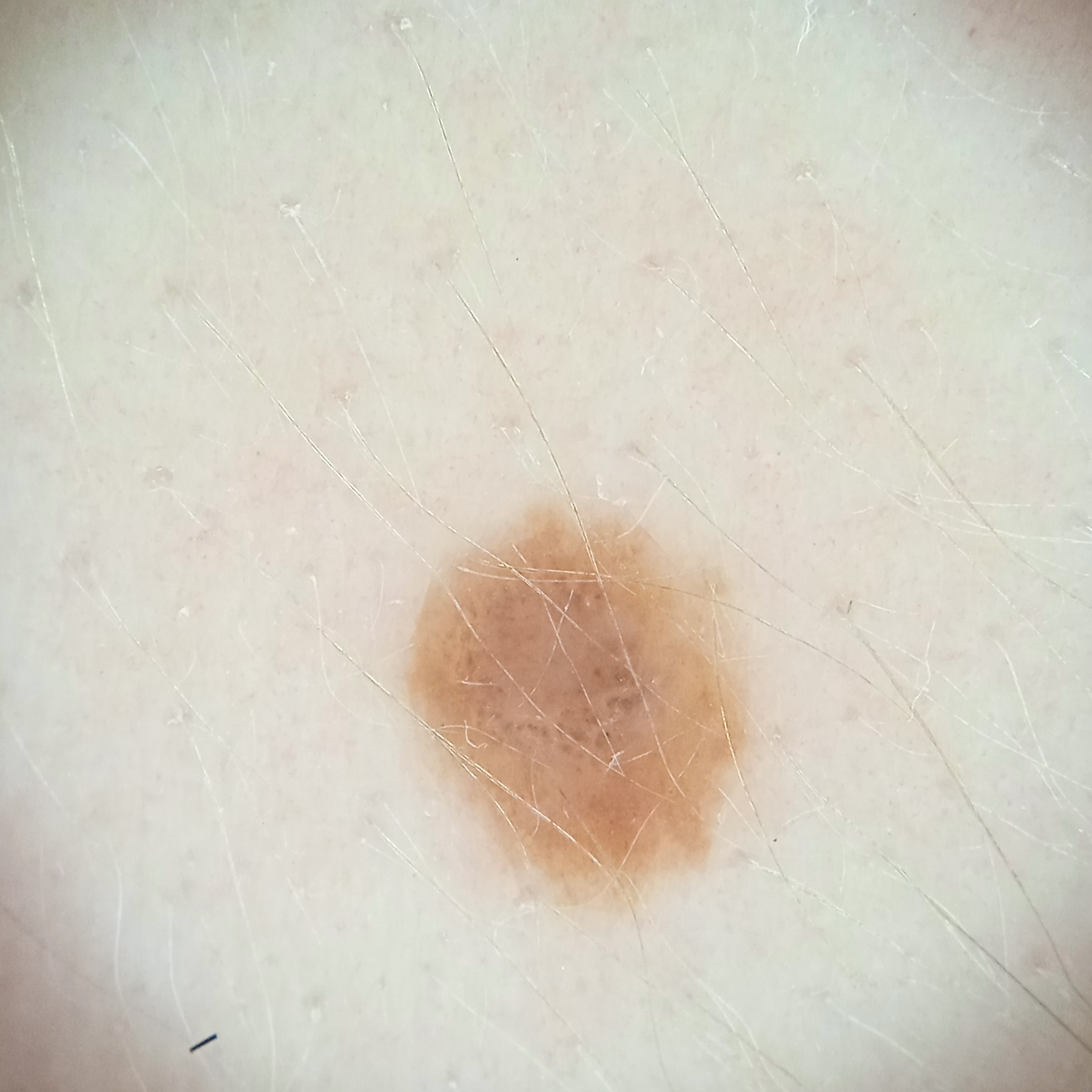  image: dermatoscopic image
  mole_burden: a moderate number of melanocytic nevi
  patient:
    age: 27
    sex: female
  sun_reaction: skin reddens with sun exposure
  lesion_location: the torso
  diagnosis:
    name: melanocytic nevus
    malignancy: benign